A dermoscopic close-up of a skin lesion:
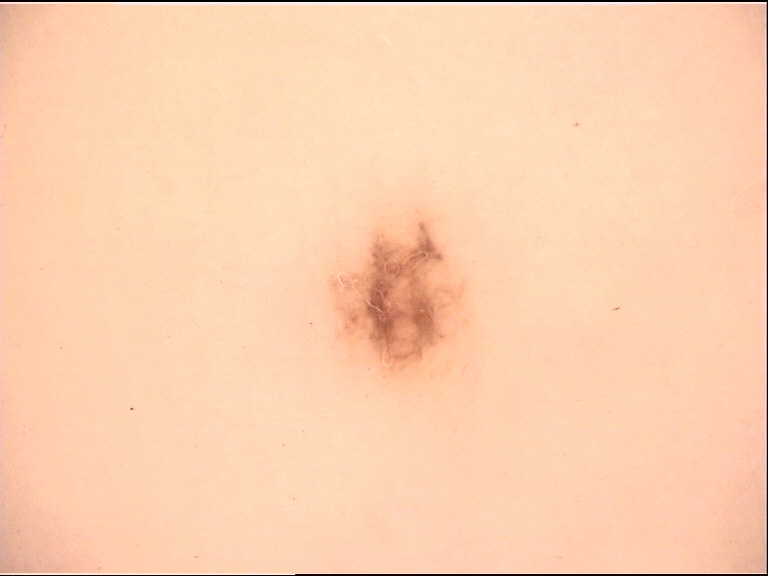lesion type=banal
class=acral junctional nevus (expert consensus)